A subject 80 years of age. A clinical photograph showing a skin lesion:
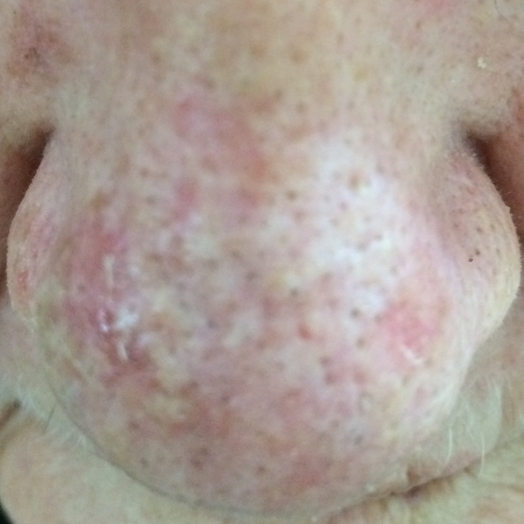By the patient's account, the lesion itches. Diagnosed by dermatologist consensus as an actinic keratosis.